A dermoscopic close-up of a skin lesion; a male subject, aged 13-17.
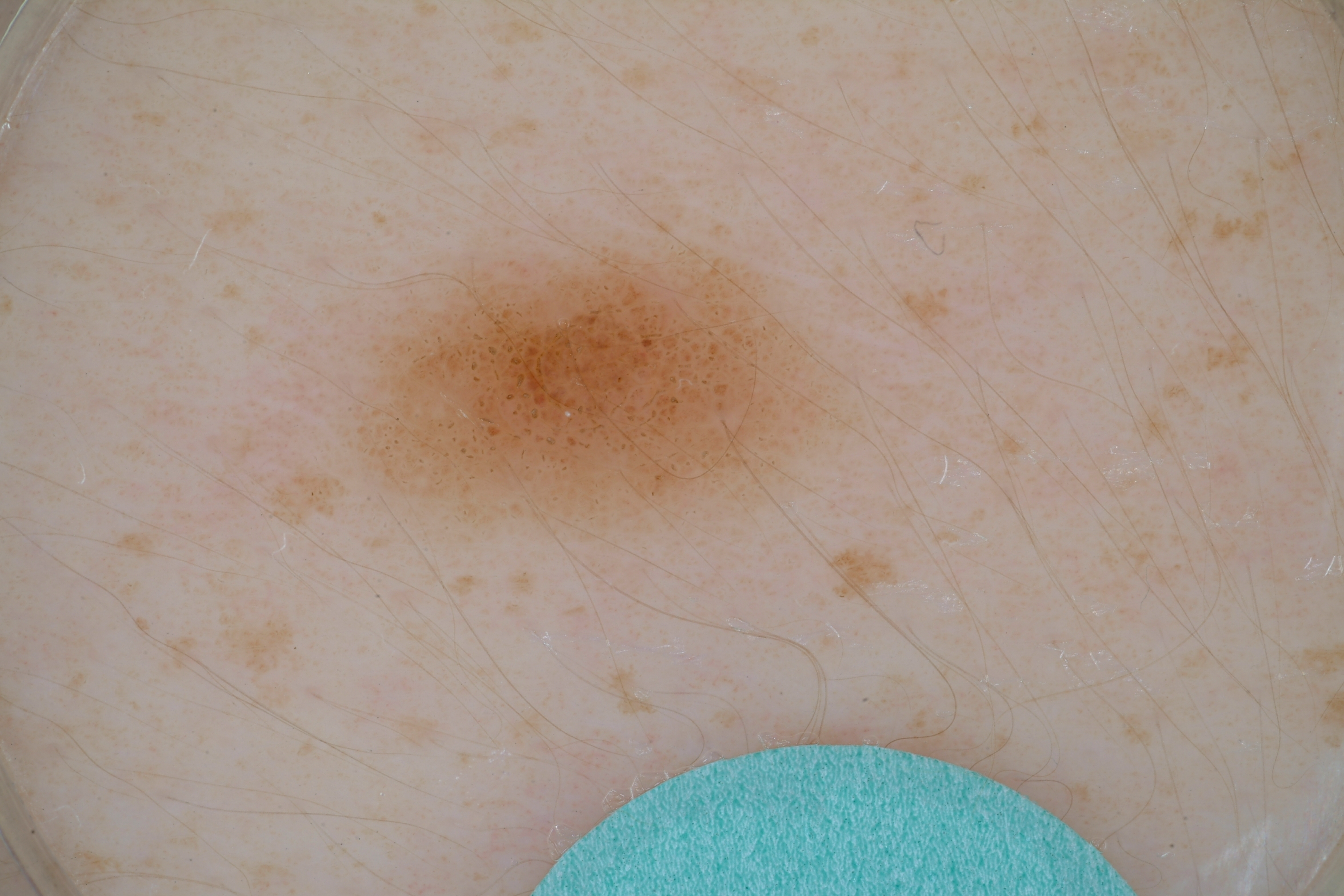Notes:
– location: box(337, 230, 879, 547)
– dermoscopic features not present: pigment network, milia-like cysts, streaks, and negative network
– diagnostic label: a melanocytic nevus, a benign skin lesion